FST III; history notes pesticide exposure and prior malignancy (patient or family); a smartphone photograph of a skin lesion; a male patient in their late 20s — 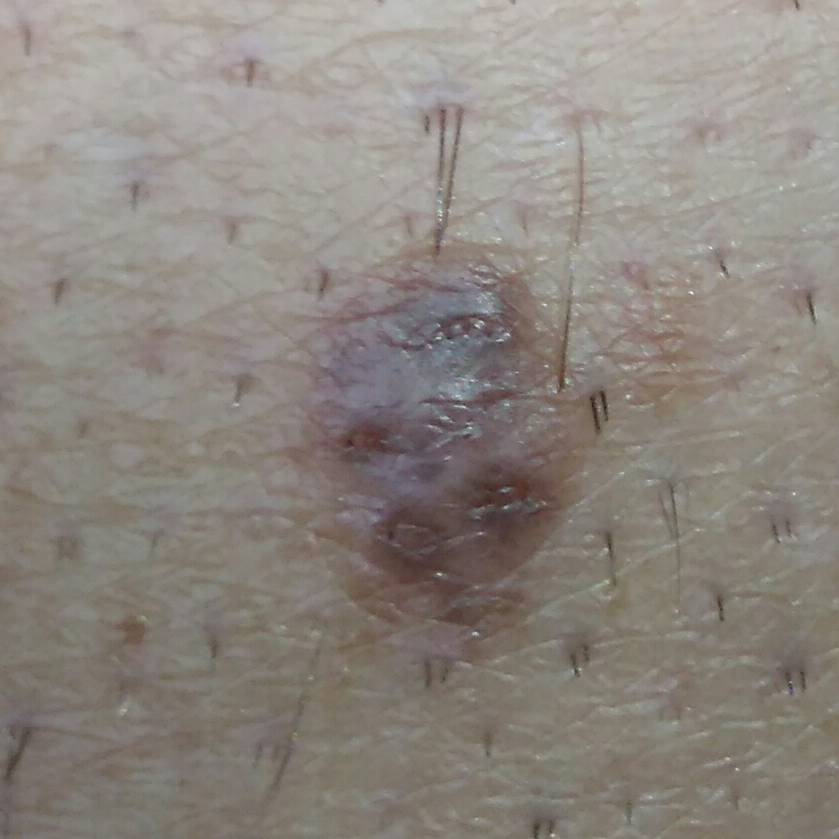| key | value |
|---|---|
| site | a thigh |
| size | 9x5 mm |
| reported symptoms | growth, elevation / no itching |
| impression | nevus (clinical consensus) |